The patient considered this a rash · skin tone: Fitzpatrick skin type IV · the contributor is 40–49, female · the lesion involves the front of the torso, arm, head or neck and palm · the patient notes the lesion is rough or flaky and raised or bumpy · the condition has been present for one to three months · a close-up photograph · the patient notes associated mouth sores and shortness of breath: 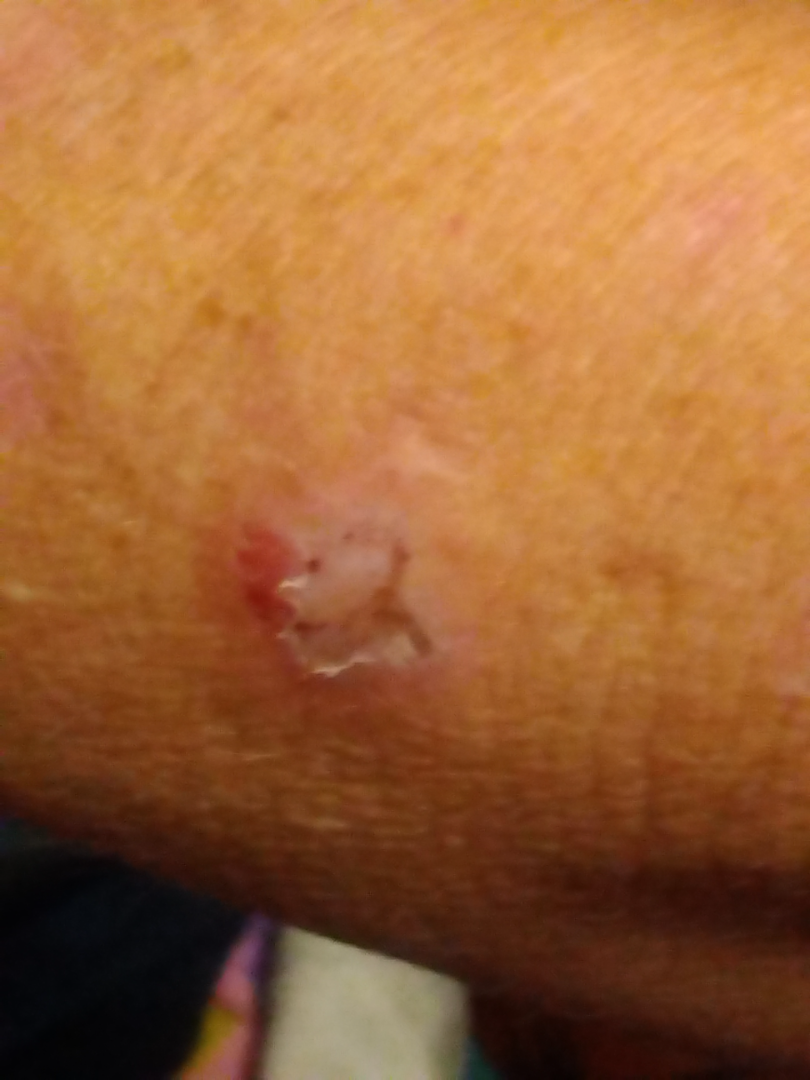Q: What was the assessment?
A: could not be assessed